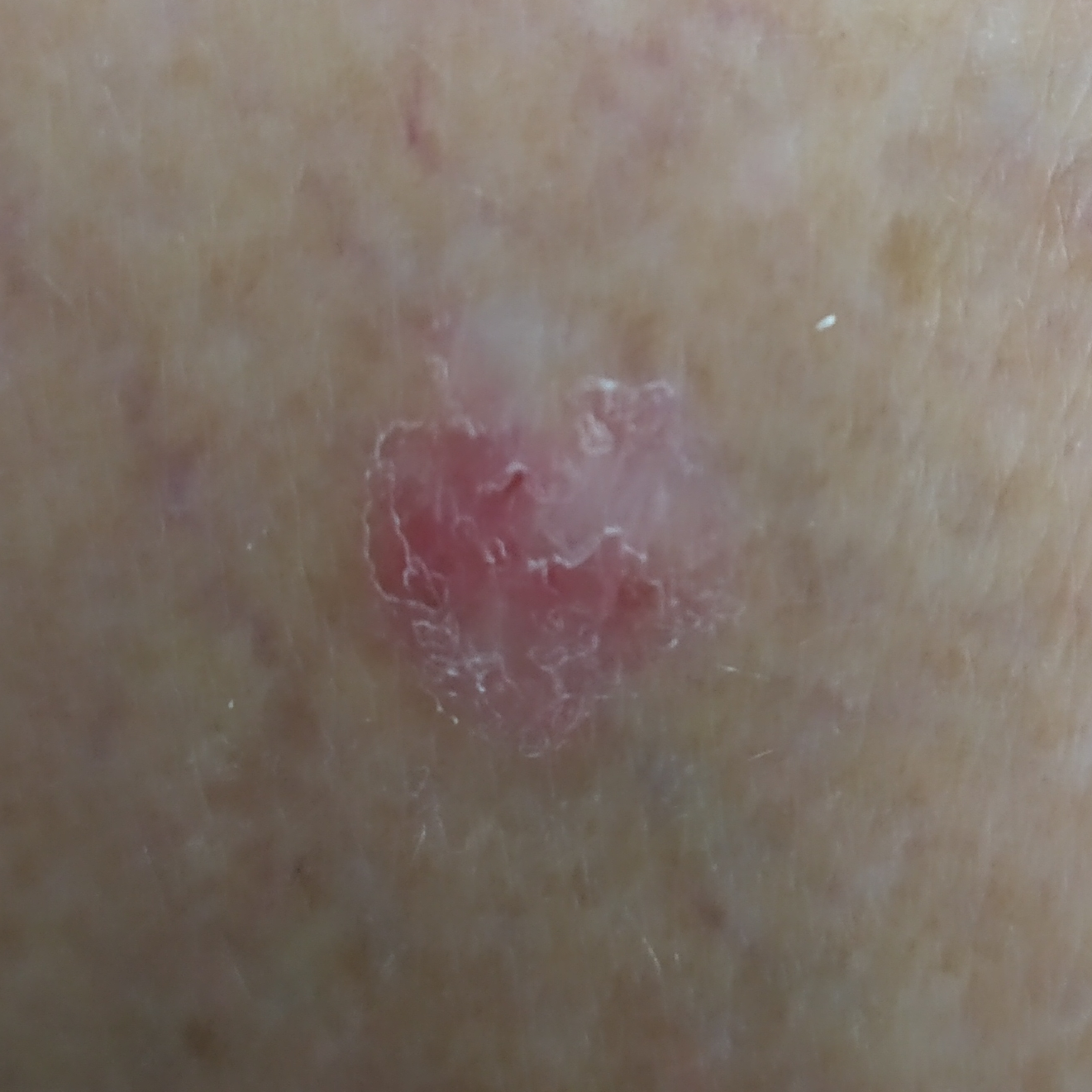Case:
– image type · clinical photo
– exposure history · prior skin cancer (patient or family), prior malignancy (patient or family), pesticide exposure
– site · a thigh
– diameter · 11x8 mm
– symptoms · bleeding, itching, growth
– diagnostic label · basal cell carcinoma (biopsy-proven)